A close-up photograph · the affected area is the arm, leg and top or side of the foot:
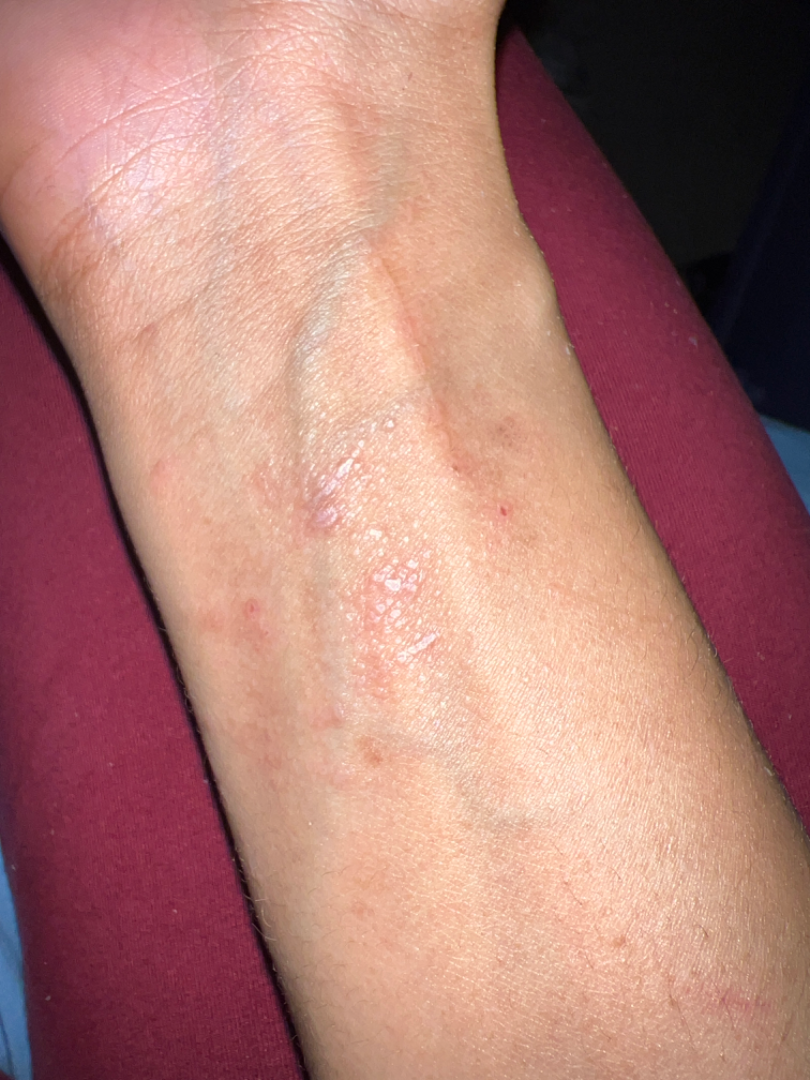Q: What is the dermatologist's impression?
A: most consistent with Allergic Contact Dermatitis